Close-up view:
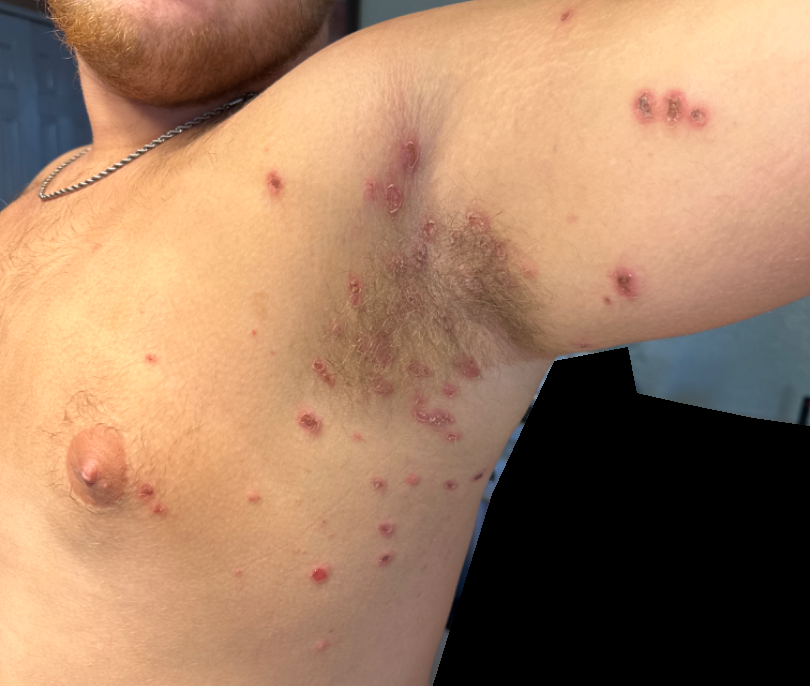{"differential": {"leading": ["Impetigo"]}}